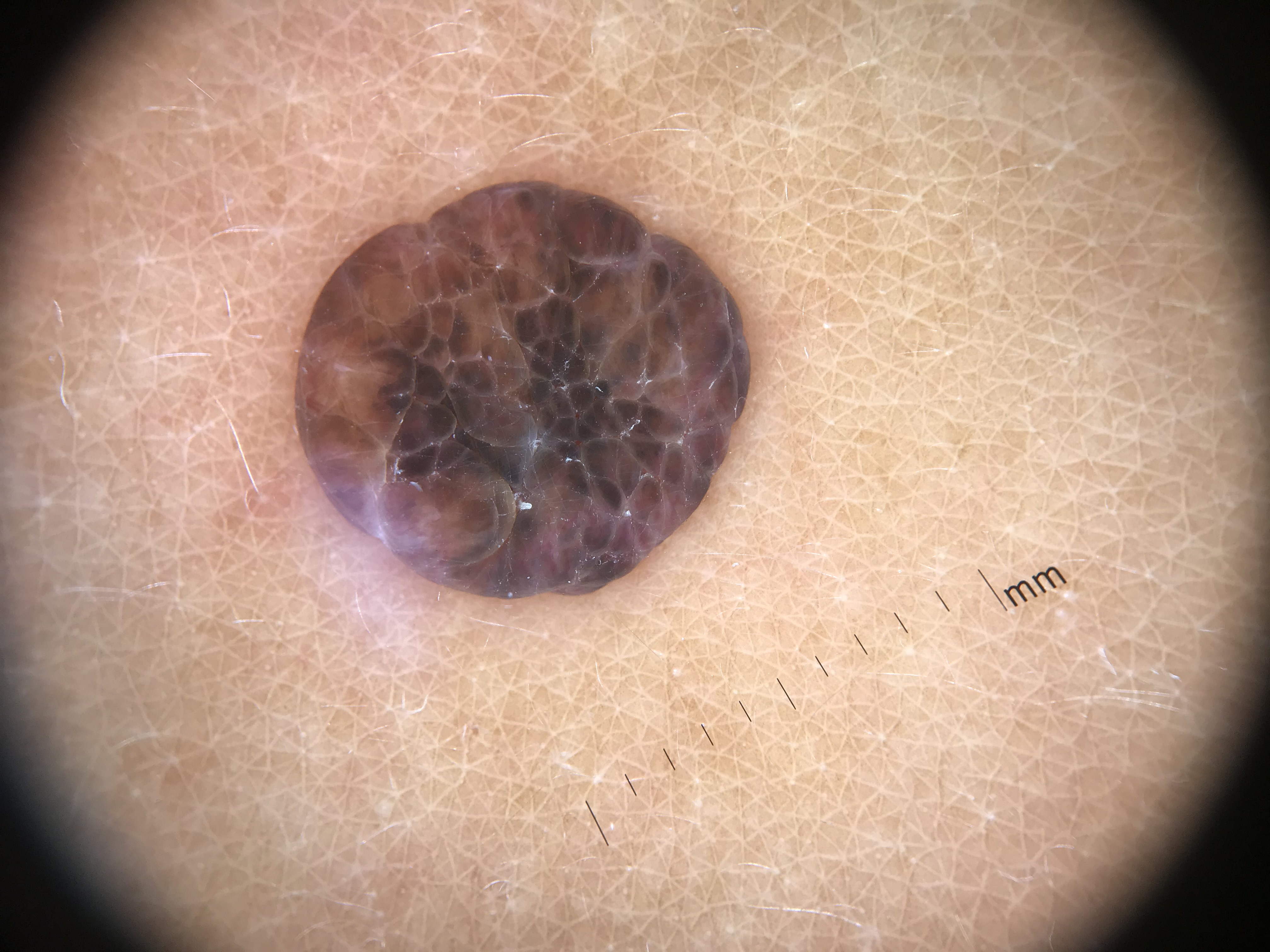Labeled as a dermal nevus.